A subject 37 years old — 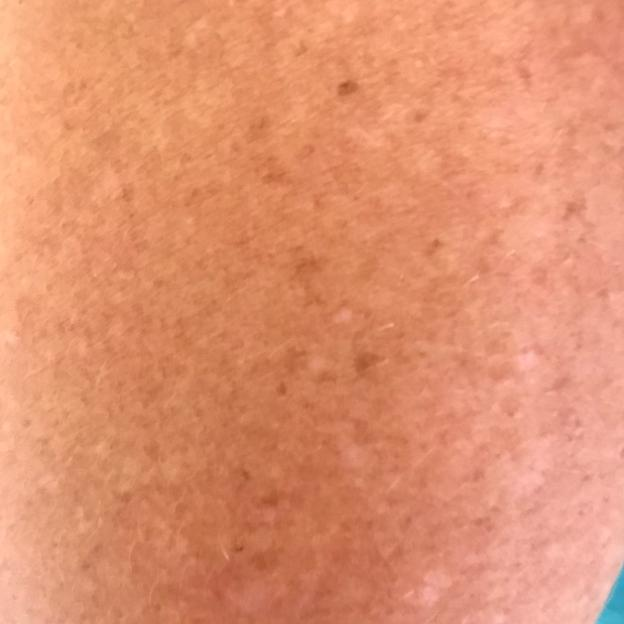Clinical context: No symptoms reported. Impression: Diagnosed by dermatologist consensus as an actinic keratosis.